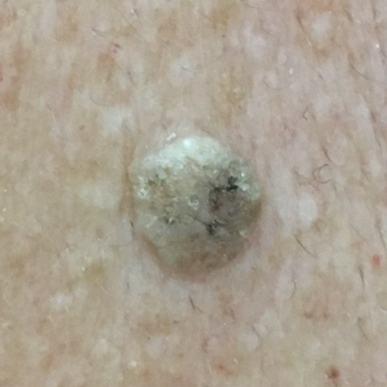  image: smartphone clinical photo
  patient:
    age: 67
  lesion_location: the back
  symptoms:
    present:
      - elevation
  diagnosis:
    name: seborrheic keratosis
    code: SEK
    malignancy: benign
    confirmation: clinical consensus